A close-up photograph · the contributor is 50–59, male:
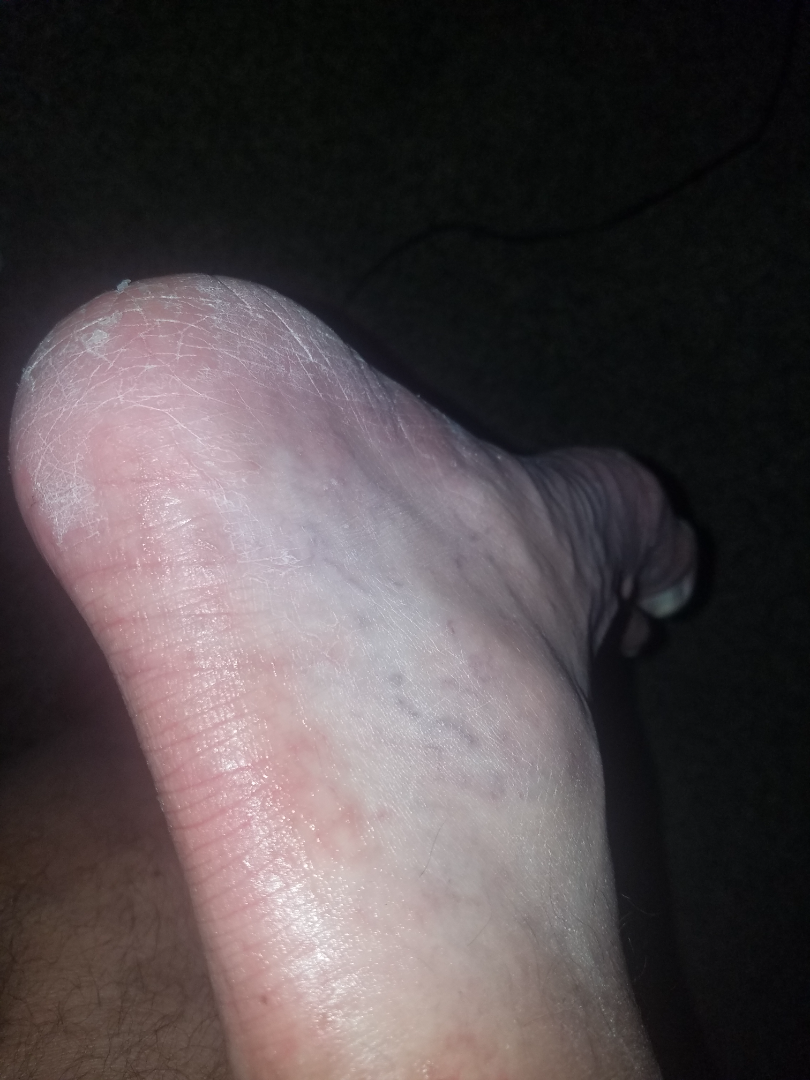<case>
  <symptoms>burning</symptoms>
  <skin_tone>
    <fitzpatrick>I</fitzpatrick>
  </skin_tone>
  <patient_category>a rash</patient_category>
  <texture>rough or flaky</texture>
  <differential>
    <leading>Tinea</leading>
    <unlikely>Eczema, Psoriasis</unlikely>
  </differential>
</case>